A skin lesion imaged with a dermatoscope: 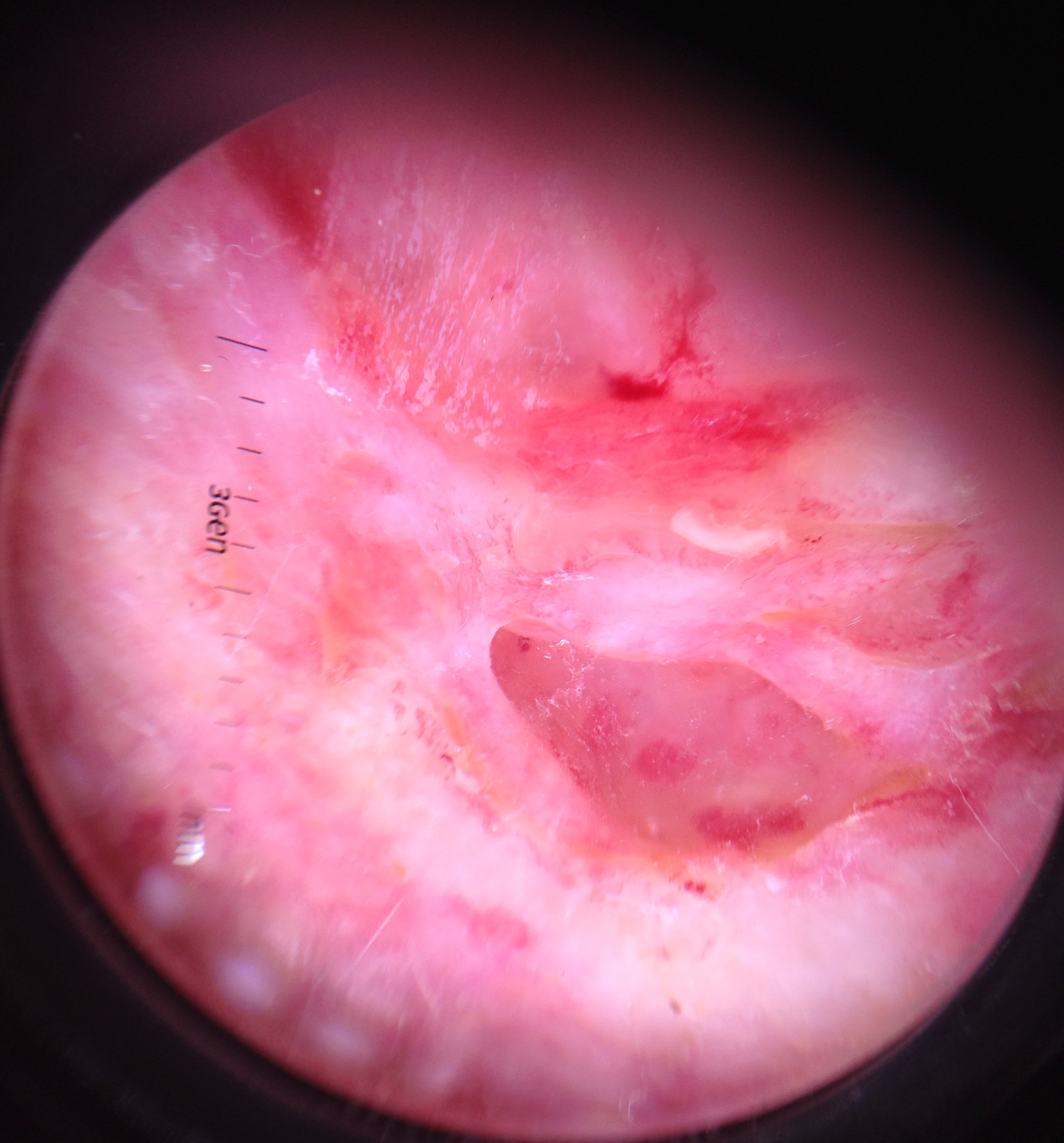subtype = keratinocytic, diagnosis = squamous cell carcinoma (biopsy-proven).